Close-up view · Fitzpatrick phototype III; lay graders estimated 2 on the MST: 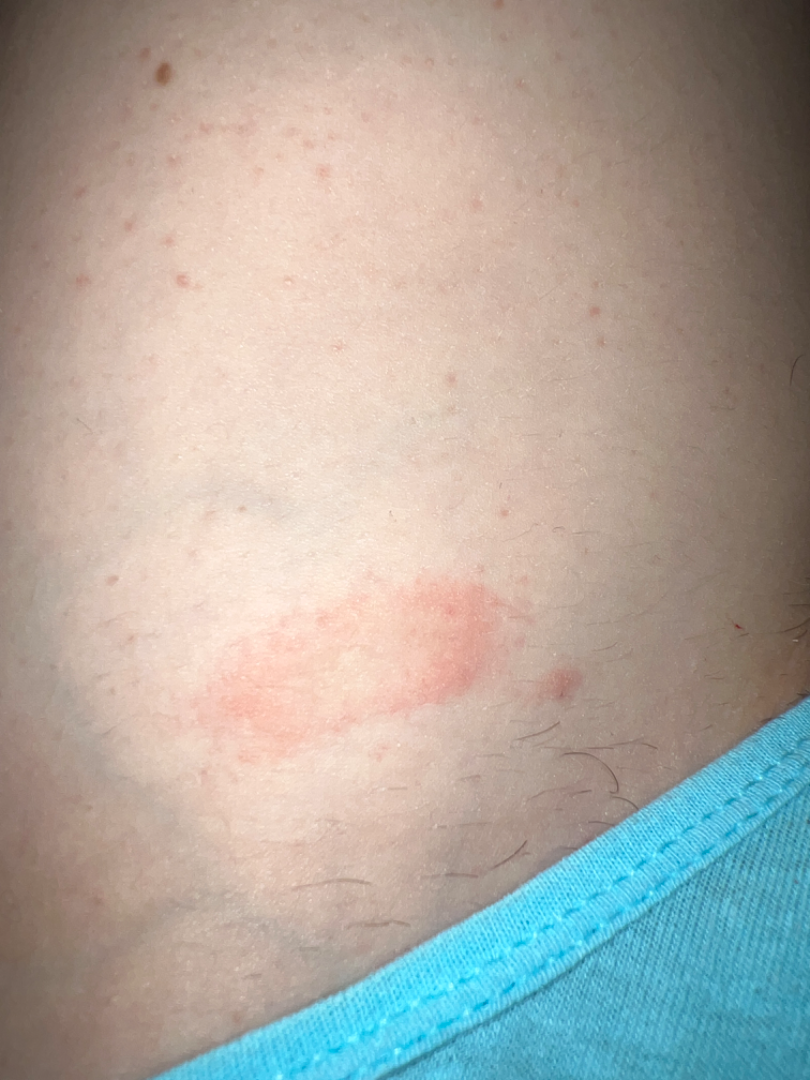The dermatologist could not determine a likely condition from the photograph alone.